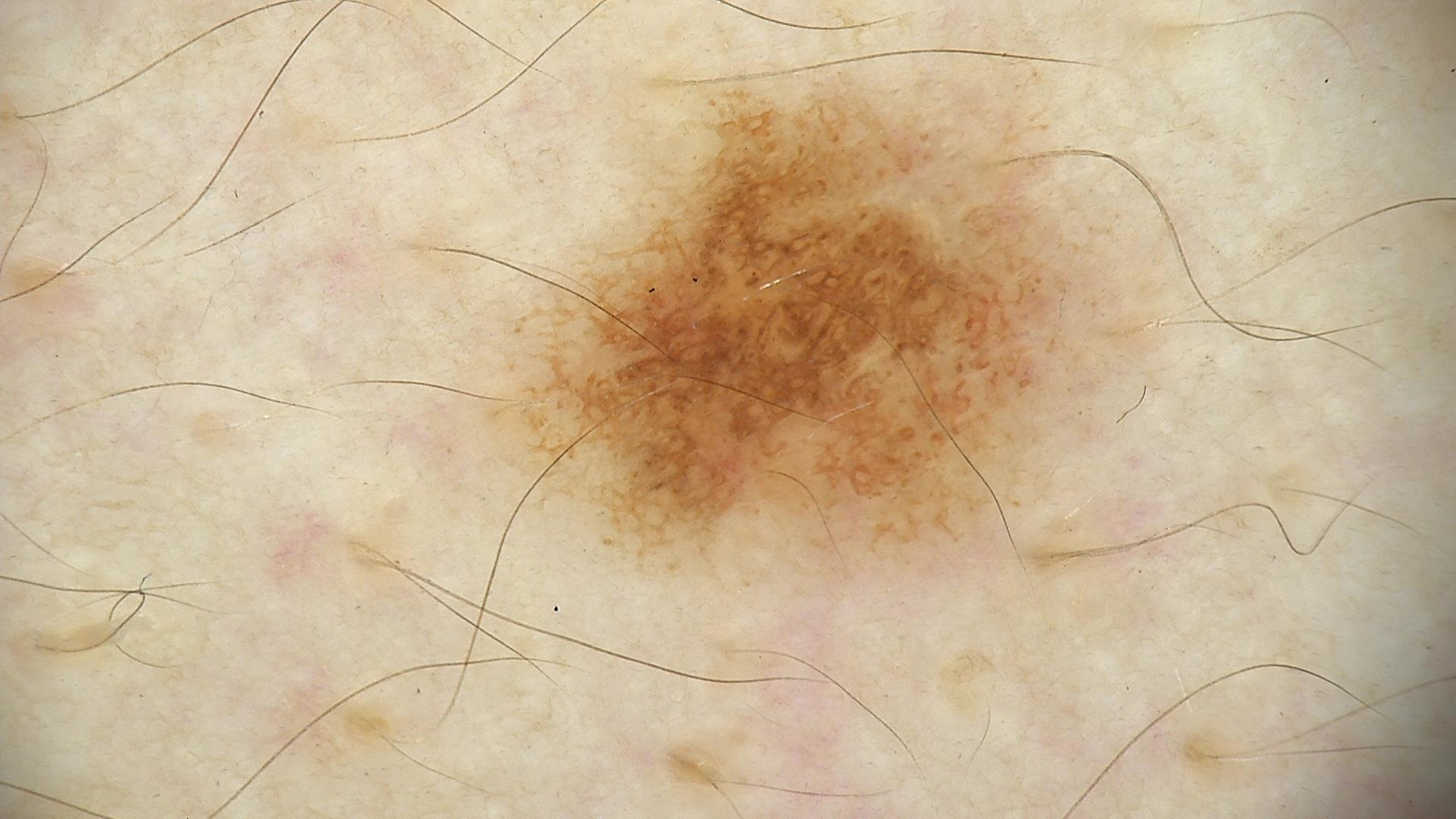Dermoscopy of a skin lesion. Consistent with a benign lesion — a dysplastic junctional nevus.